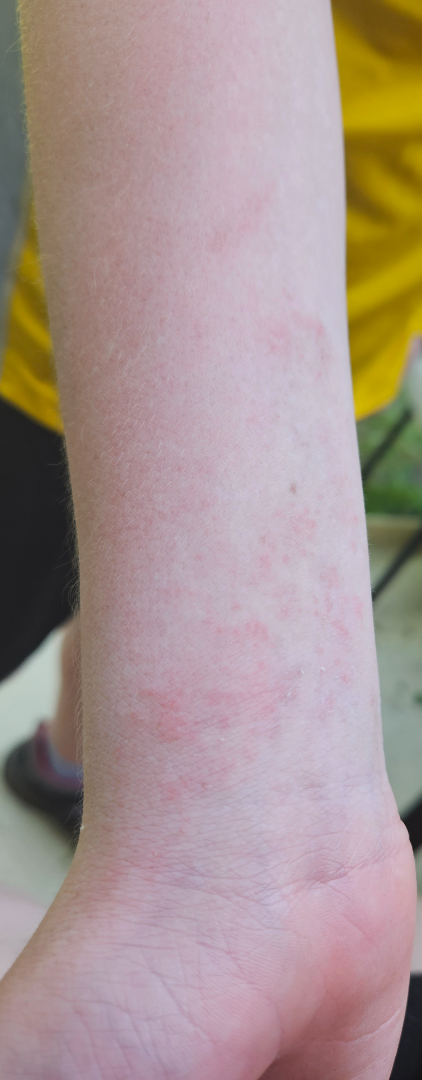Q: How long has this been present?
A: about one day
Q: What is the affected area?
A: arm
Q: What is the framing?
A: at an angle
Q: What conditions are considered?
A: the primary impression is Eczema; possibly Allergic Contact Dermatitis